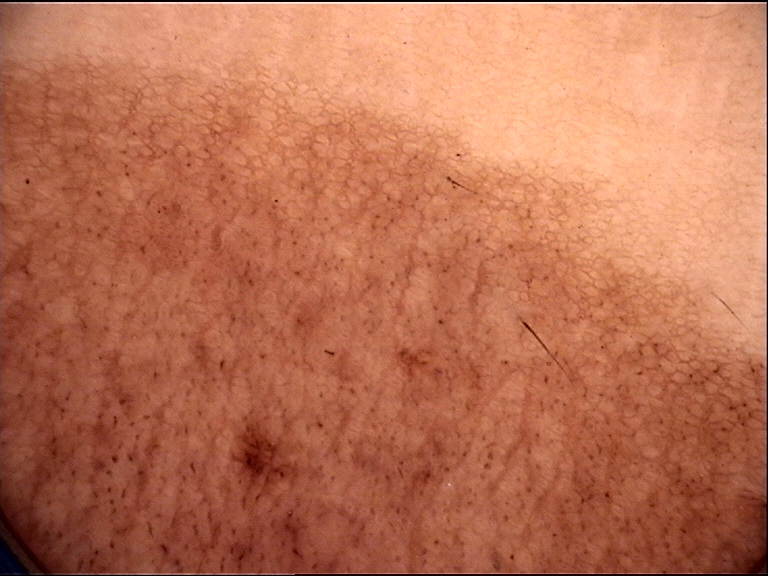{"image": "dermatoscopy", "lesion_type": {"main_class": "banal", "pattern": "junctional"}, "diagnosis": {"name": "congenital junctional nevus", "code": "cjb", "malignancy": "benign", "super_class": "melanocytic", "confirmation": "expert consensus"}}